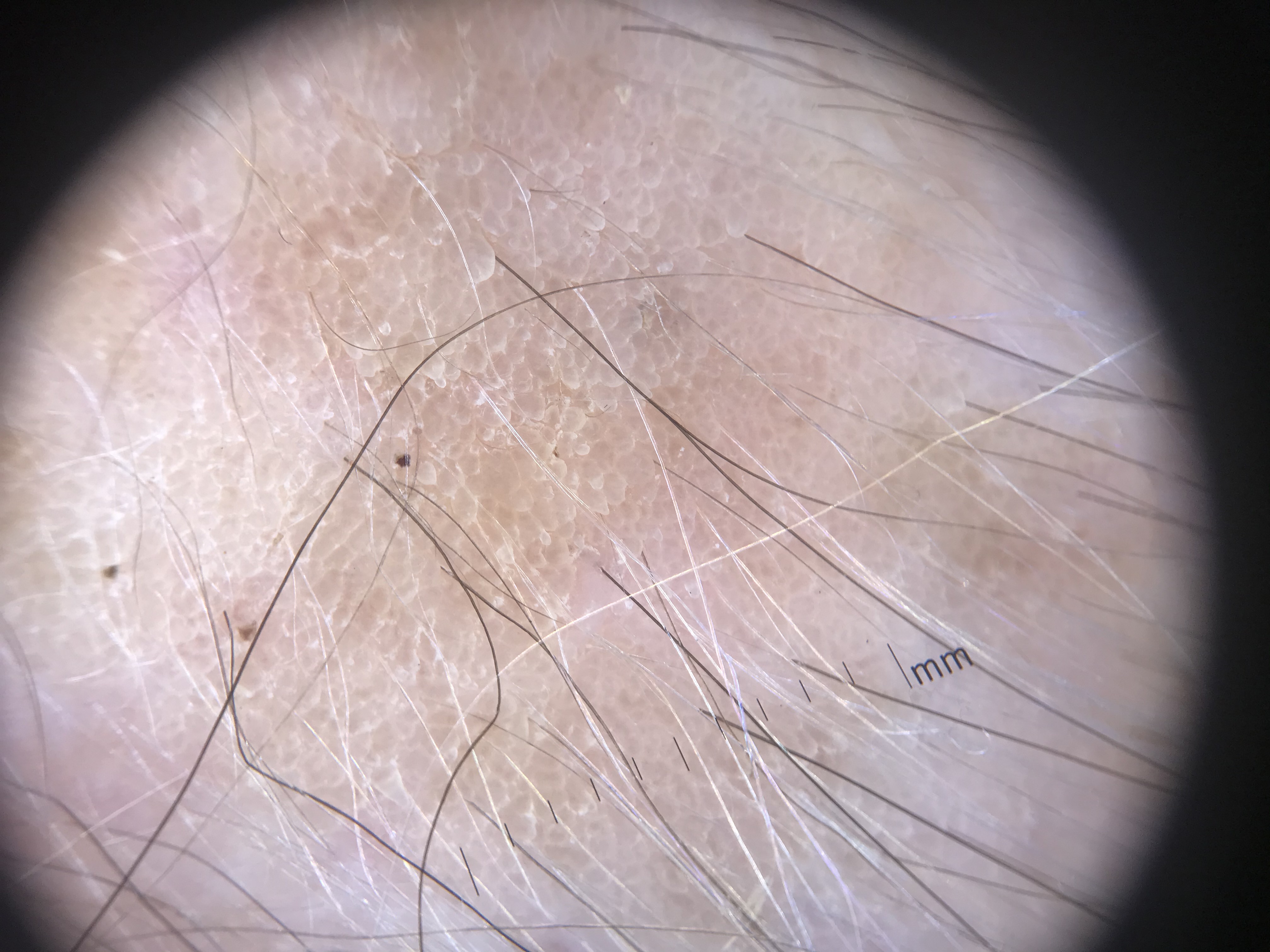Consistent with a keratinocytic lesion — a seborrheic keratosis.